A dermatoscopic image of a skin lesion.
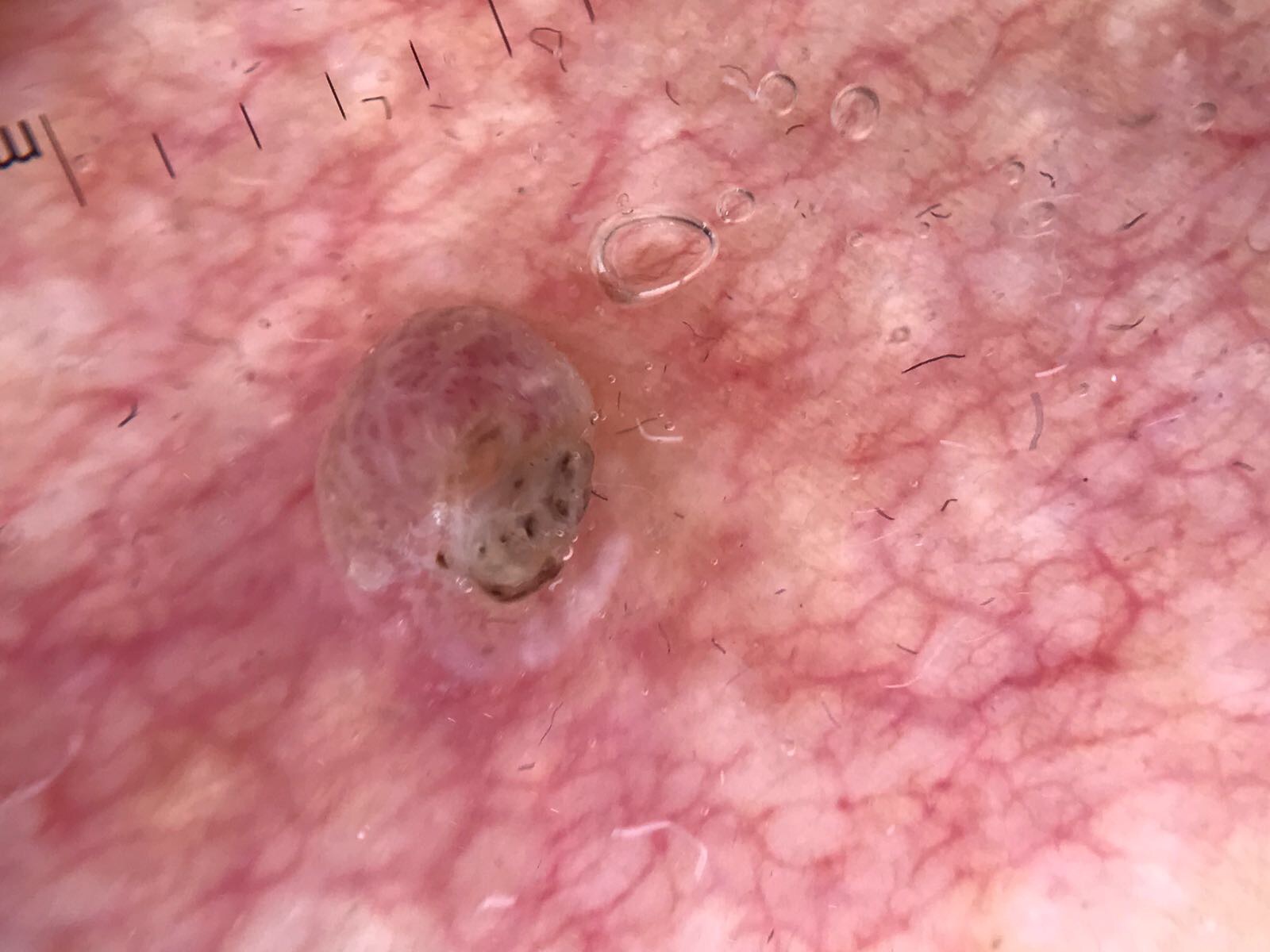Case:
* diagnostic label: squamous cell carcinoma (biopsy-proven)